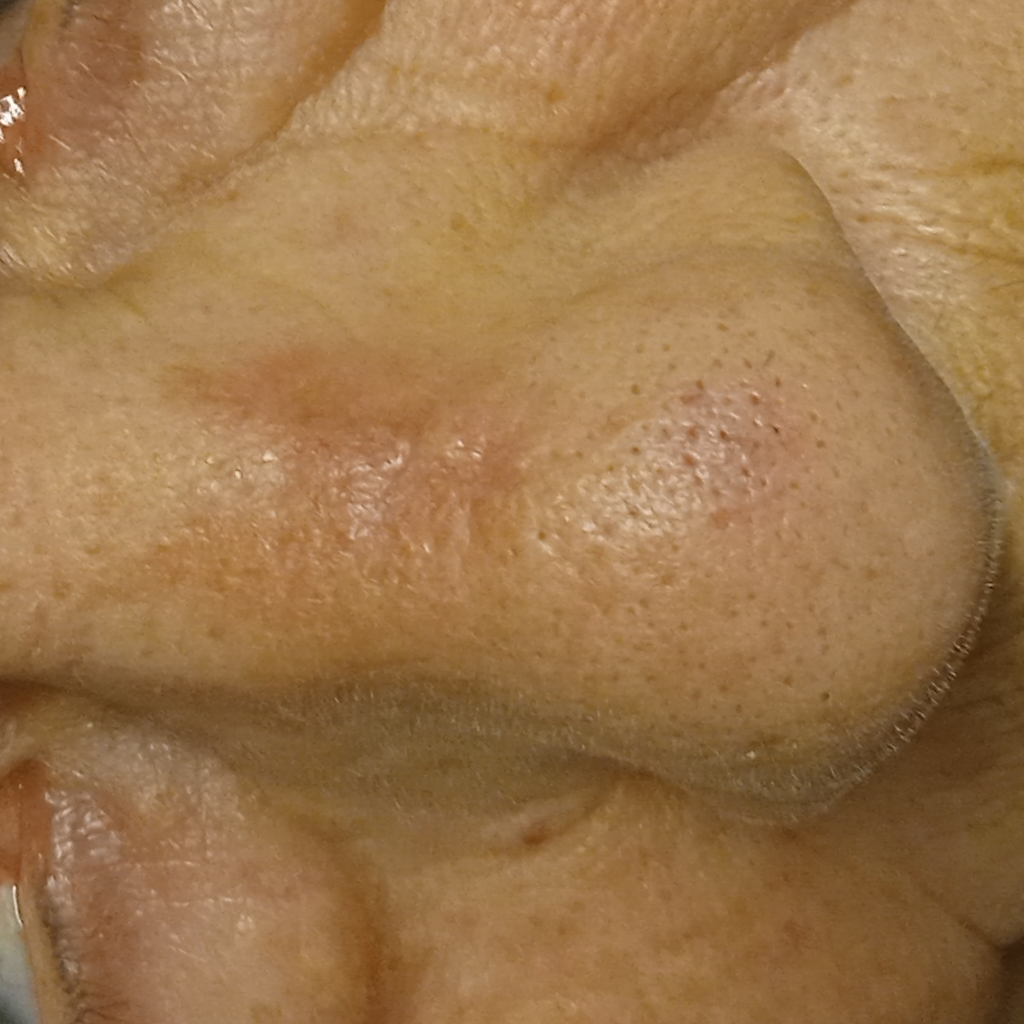<record>
  <image>clinical photo</image>
  <patient>
    <age>68</age>
    <sex>female</sex>
  </patient>
  <sun_reaction>skin tans without first burning</sun_reaction>
  <mole_burden>few melanocytic nevi overall</mole_burden>
  <risk_factors>
    <negative>no prior organ transplant</negative>
  </risk_factors>
  <referral>research study (no referral diagnosis)</referral>
  <lesion_location>the face</lesion_location>
  <lesion_size>
    <diameter_mm>9.9</diameter_mm>
  </lesion_size>
  <diagnosis>
    <name>actinic keratosis</name>
    <malignancy>benign</malignancy>
  </diagnosis>
</record>